A dermoscopic image of a skin lesion: 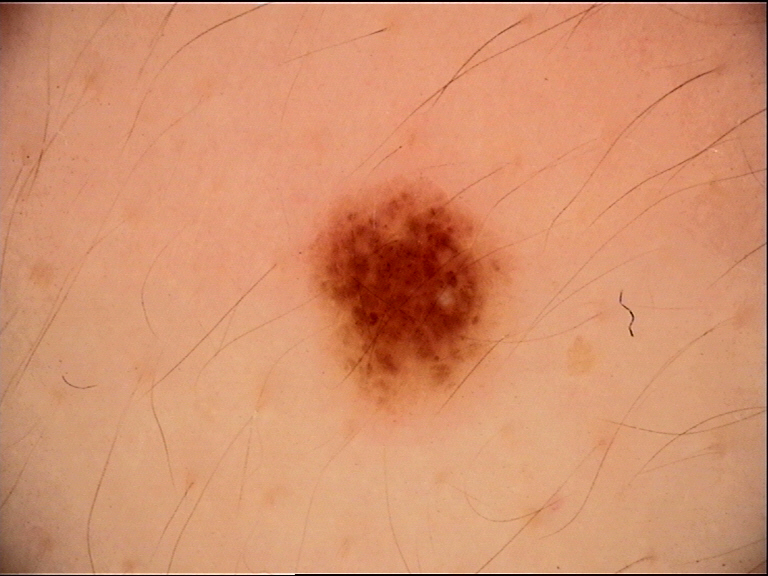Classified as a benign lesion — a dysplastic compound nevus.